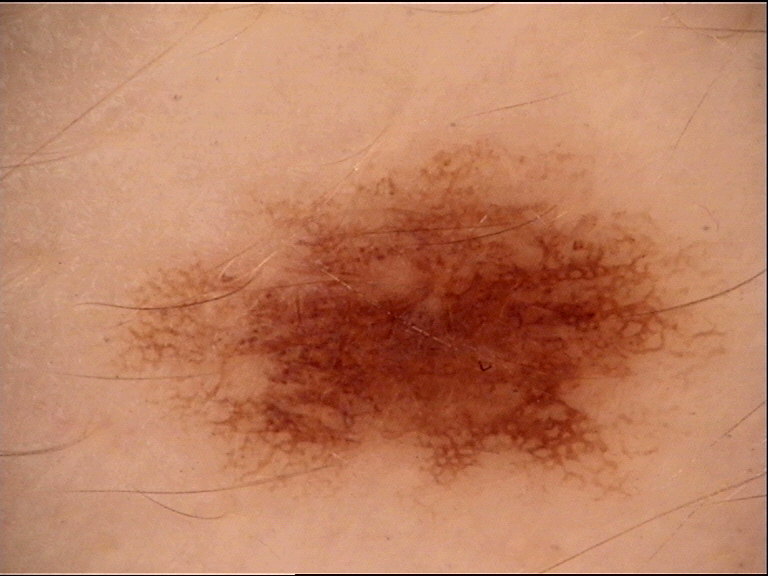<dermoscopy>
  <image>dermatoscopy</image>
  <diagnosis>
    <name>dysplastic junctional nevus</name>
    <code>jd</code>
    <malignancy>benign</malignancy>
    <super_class>melanocytic</super_class>
    <confirmation>expert consensus</confirmation>
  </diagnosis>
</dermoscopy>